The patient reports the condition has been present for less than one week · no associated systemic symptoms reported · the affected area is the arm, front of the torso, head or neck and leg · the patient considered this a rash · a close-up photograph · the lesion is described as flat · Fitzpatrick phototype II; lay graders estimated MST 3 (US pool) or 2 (India pool) · symptoms reported: itching and bleeding · female subject, age 18–29 — 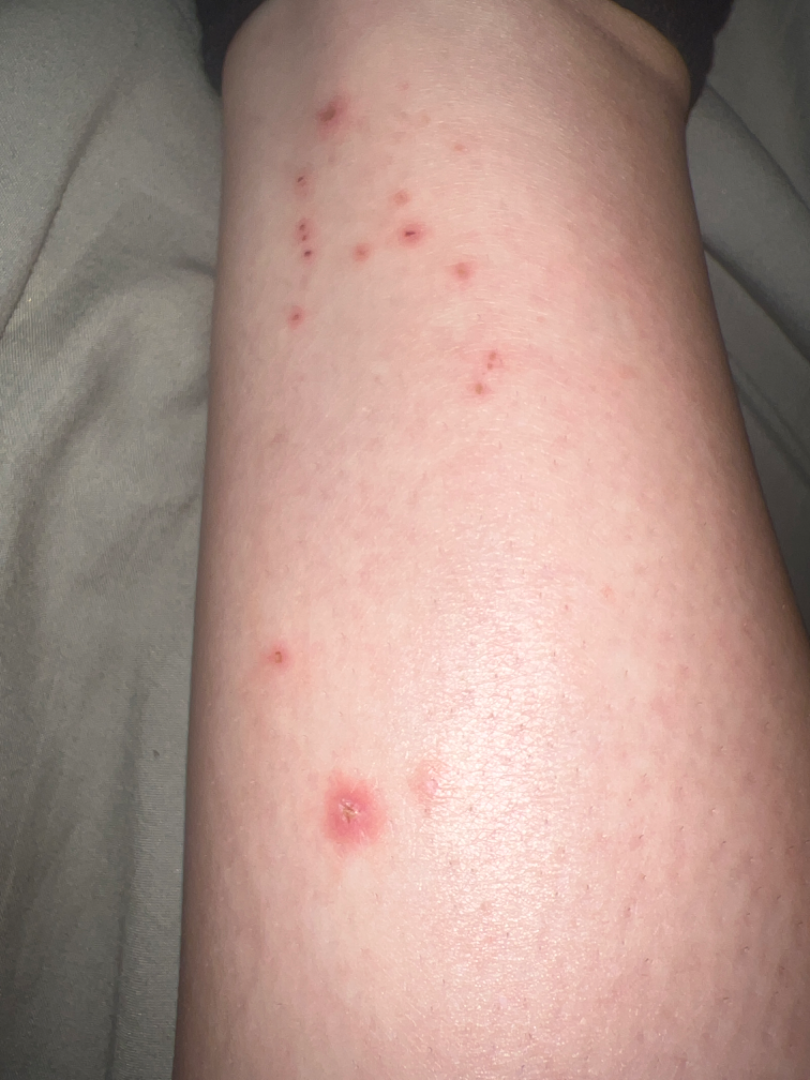Most likely Insect Bite; possibly Eczema; an alternative is Molluscum Contagiosum; less likely is Allergic Contact Dermatitis; a remote consideration is Abrasion, scrape, or scab.